A dermoscopic image of a skin lesion, the subject is a female aged 58 to 62.
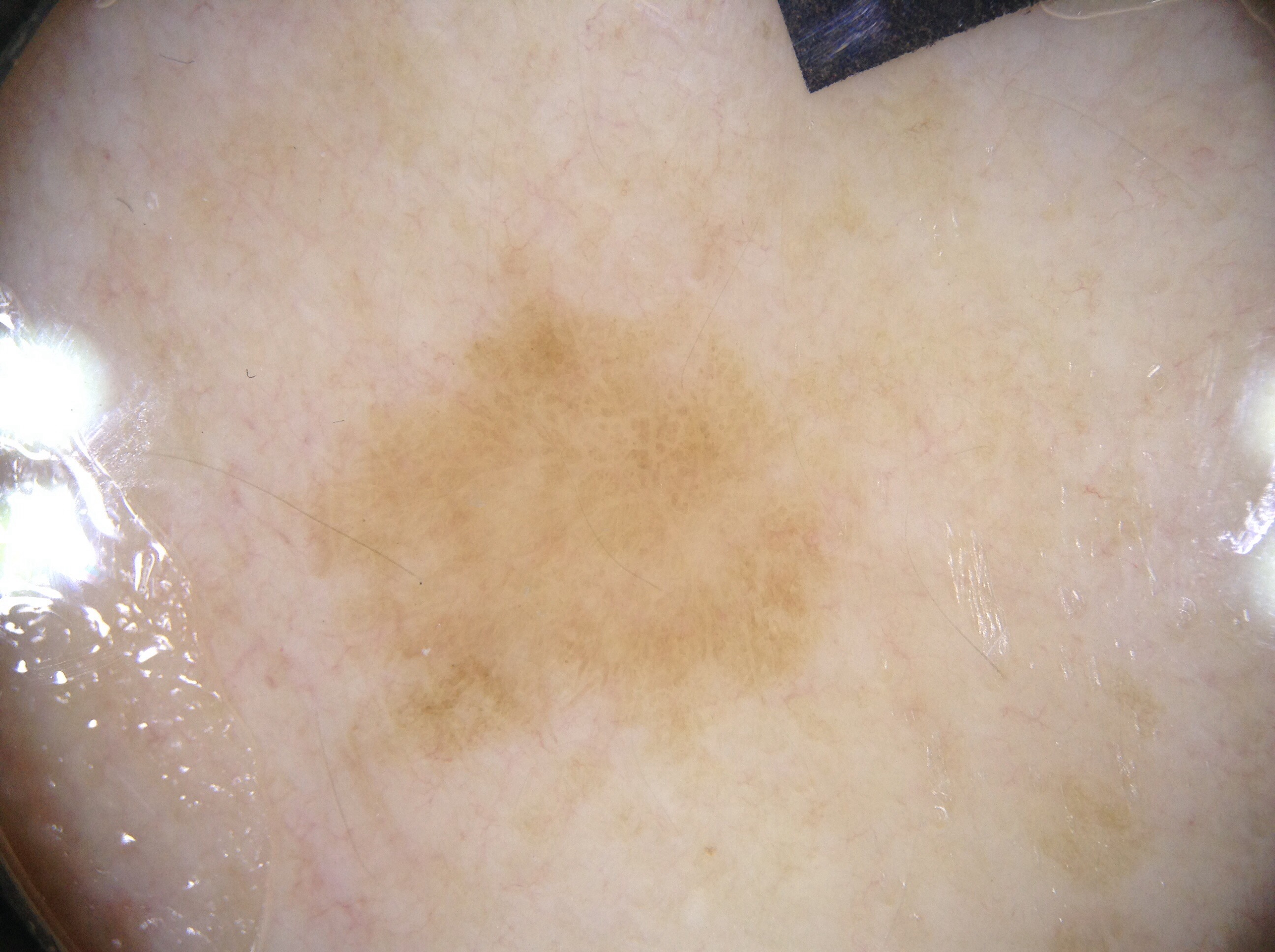<record>
  <dermoscopic_features>
    <present>milia-like cysts, negative network</present>
    <absent>pigment network, streaks</absent>
  </dermoscopic_features>
  <lesion_extent>moderate</lesion_extent>
  <lesion_location>
    <bbox_xyxy>319, 297, 827, 743</bbox_xyxy>
  </lesion_location>
  <diagnosis>
    <name>seborrheic keratosis</name>
    <malignancy>benign</malignancy>
    <lineage>keratinocytic</lineage>
    <provenance>clinical</provenance>
  </diagnosis>
</record>